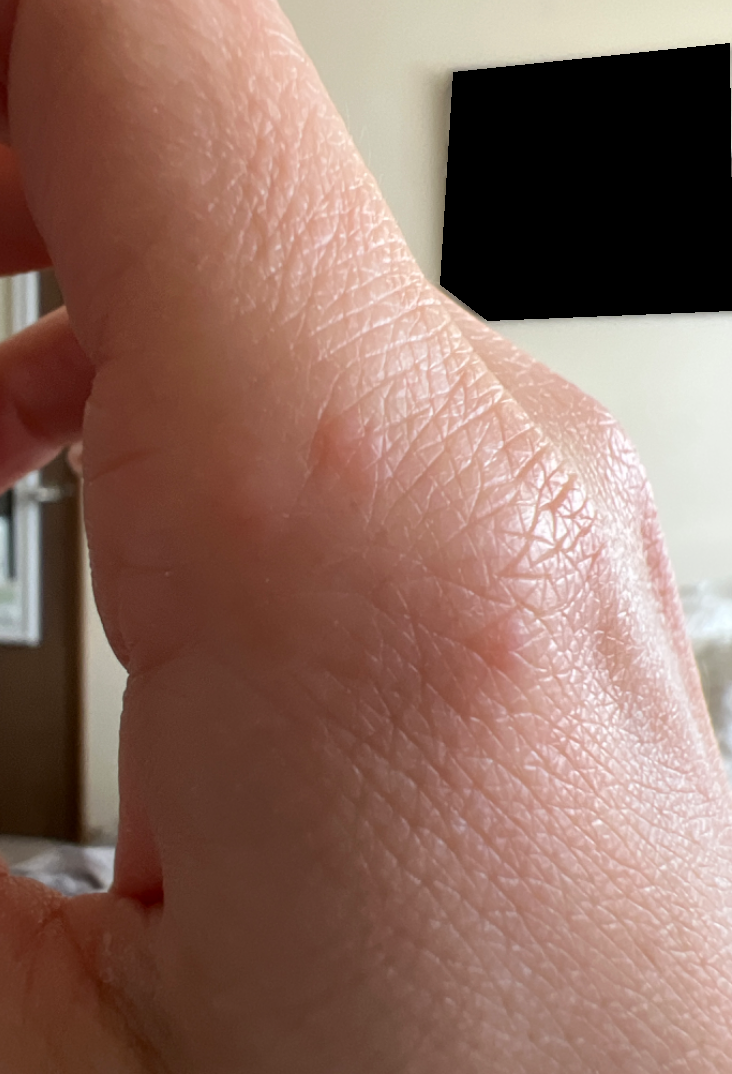Findings:
On remote dermatologist review, Insect Bite (primary); Urticaria (considered); Allergic Contact Dermatitis (considered).